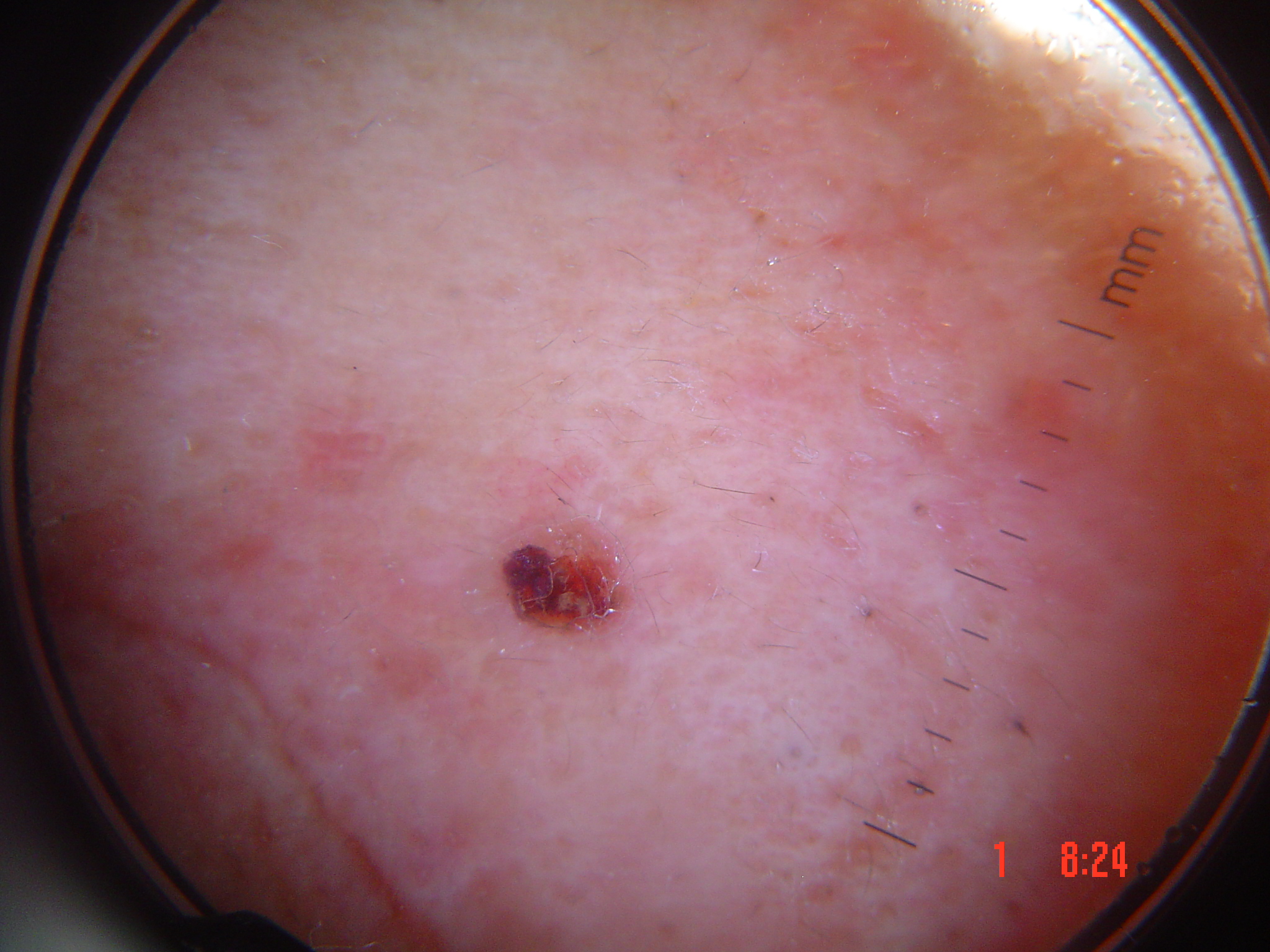Findings:
A dermatoscopic image of a skin lesion.
Pathology:
Biopsy-confirmed as a keratinocytic, malignant lesion — a squamous cell carcinoma.